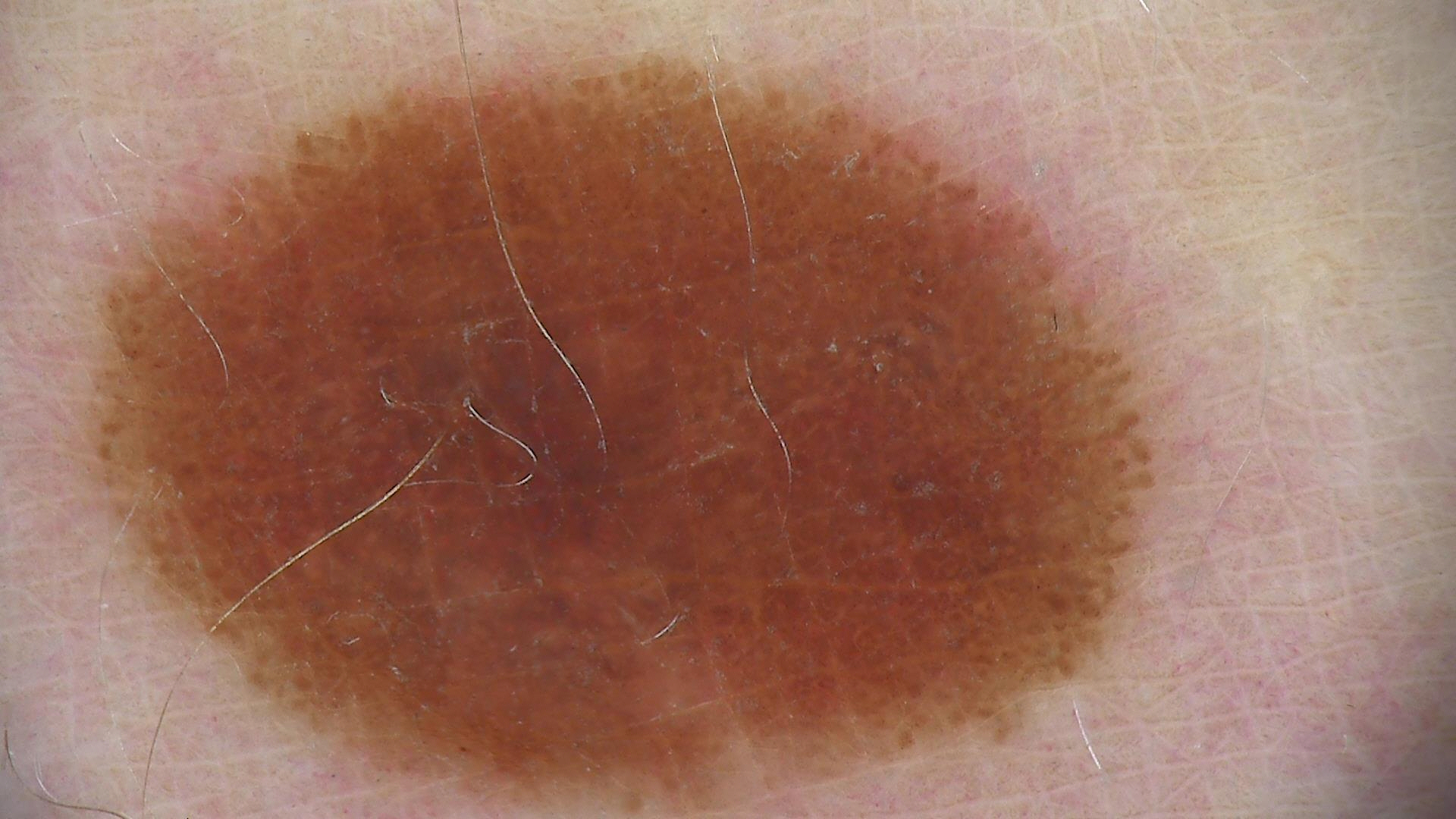Conclusion:
Diagnosed as a dysplastic junctional nevus.